A male patient 68 years of age — 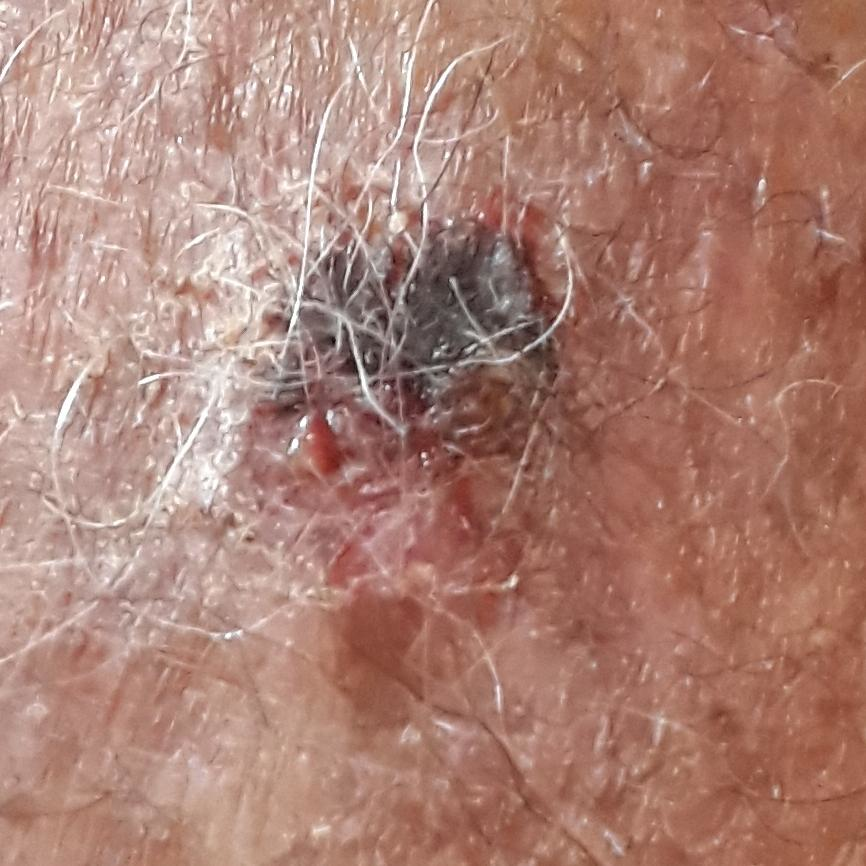Located on a forearm. By the patient's account, the lesion has grown, has bled, itches, and is elevated. The biopsy diagnosis was a basal cell carcinoma.